Dermoscopy of a skin lesion.
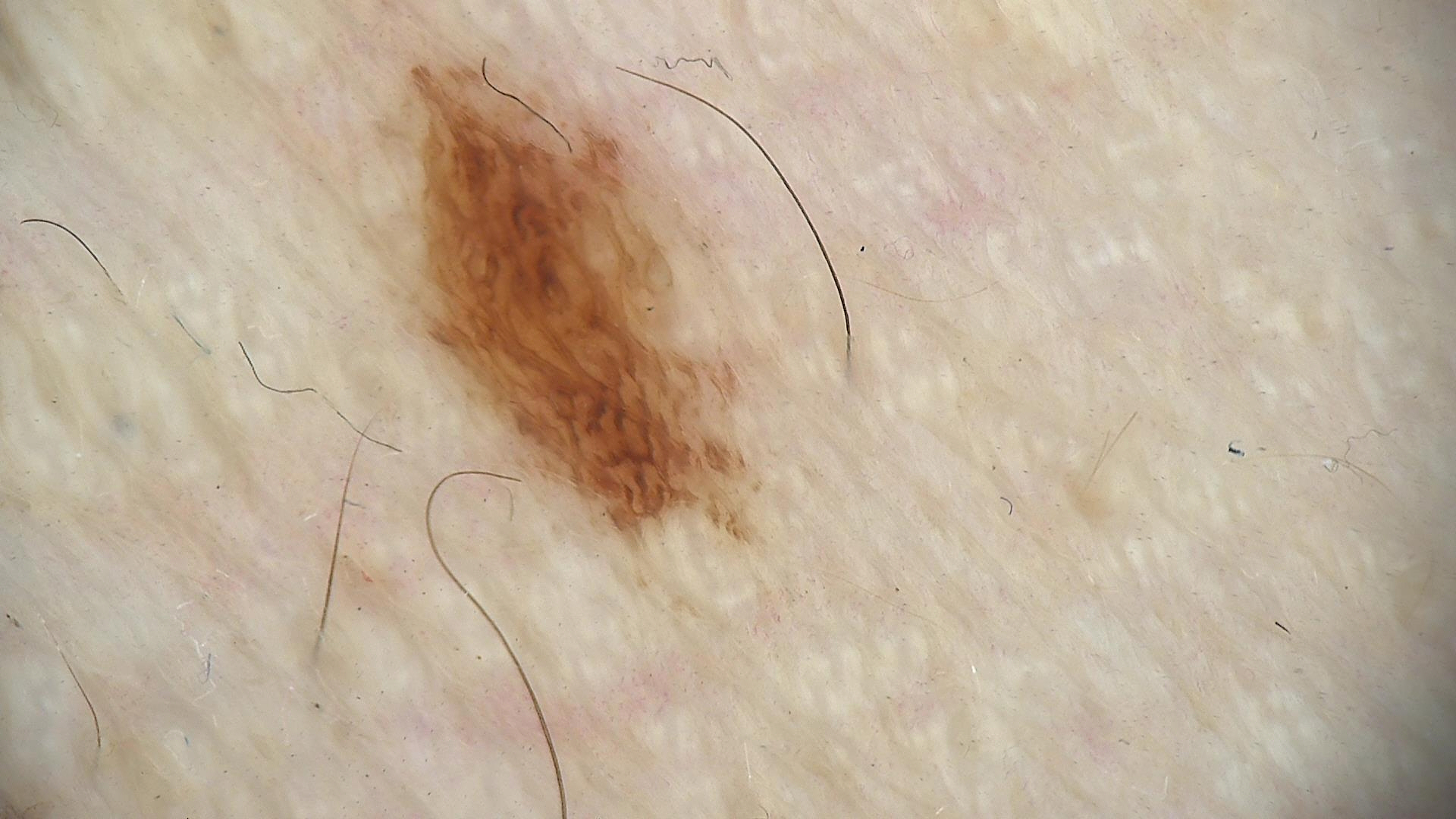diagnosis: dysplastic junctional nevus (expert consensus)